Dermoscopy of a skin lesion, the patient is a male approximately 25 years of age.
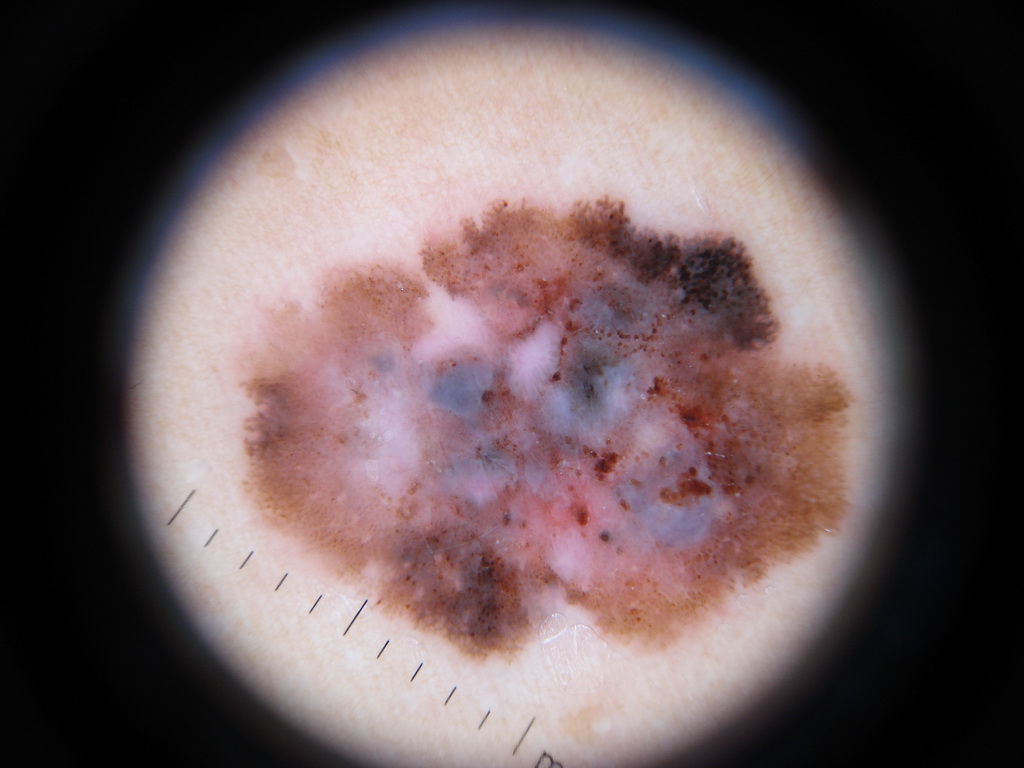{
  "dermoscopic_features": {
    "present": [
      "pigment network",
      "streaks",
      "negative network"
    ],
    "absent": [
      "milia-like cysts",
      "globules"
    ]
  },
  "lesion_location": {
    "bbox_xyxy": [
      236,
      195,
      862,
      672
    ]
  },
  "diagnosis": {
    "name": "melanoma",
    "malignancy": "malignant",
    "lineage": "melanocytic",
    "provenance": "histopathology"
  }
}